A dermoscopy image of a single skin lesion; a male patient, roughly 60 years of age — 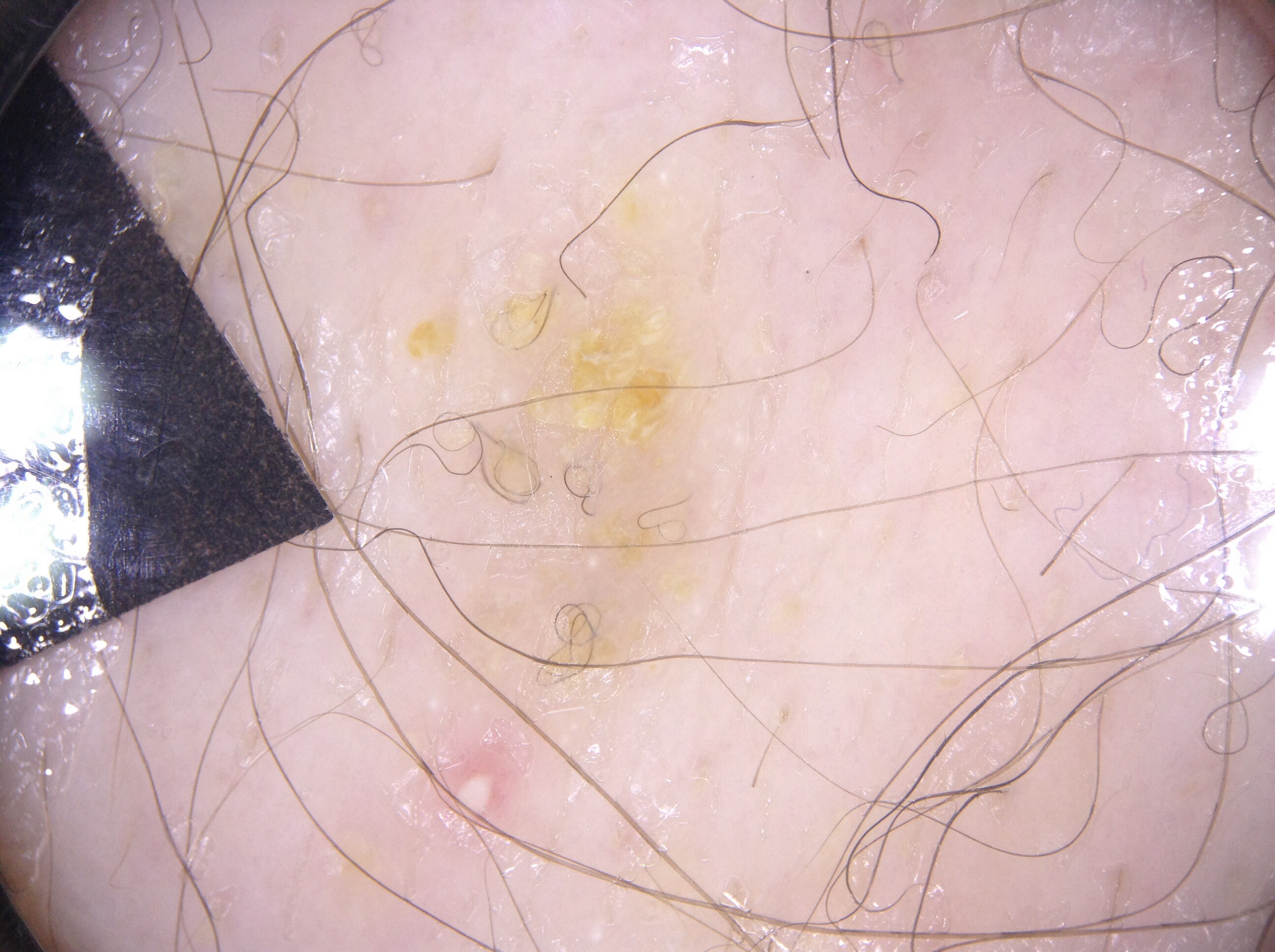The lesion takes up about 22% of the image. Dermoscopic assessment notes milia-like cysts. The lesion is bounded by left=357, top=44, right=799, bottom=867. The diagnostic assessment was a seborrheic keratosis, a benign lesion.